A close-up photograph. Located on the leg:
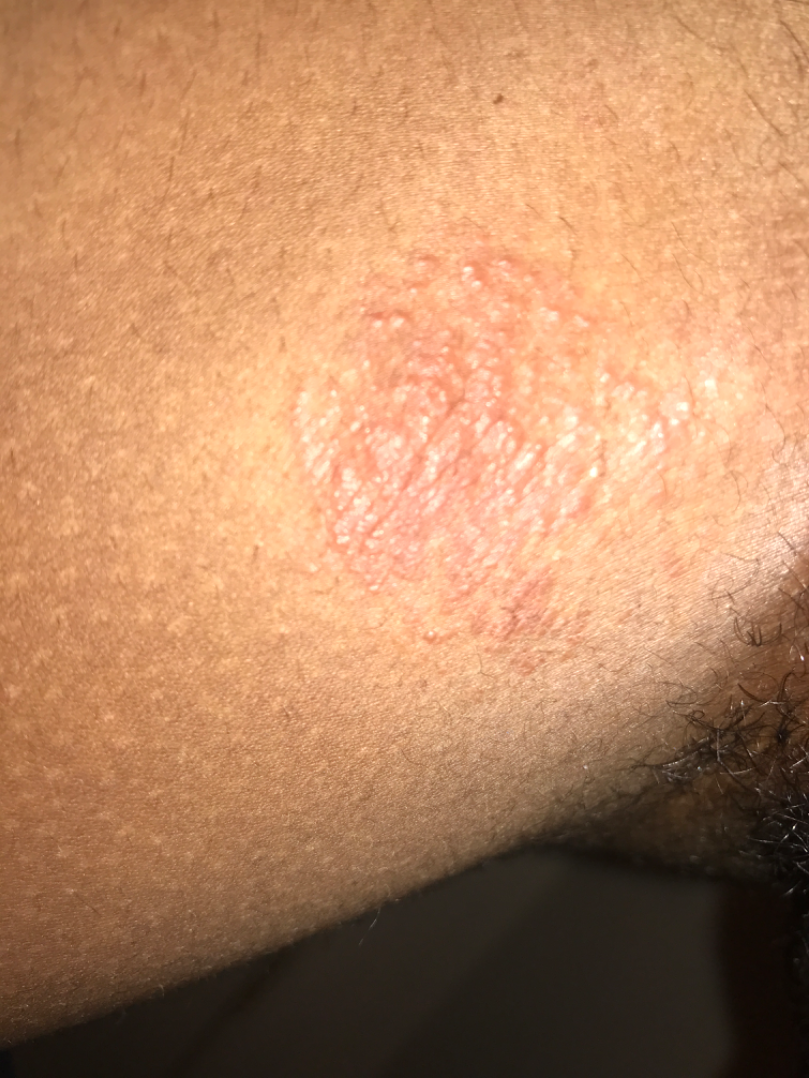Background:
Skin tone: Fitzpatrick V; non-clinician graders estimated Monk skin tone scale 4 or 5 (two reviewer pools). Self-categorized by the patient as a rash. Texture is reported as raised or bumpy. Reported duration is less than one week. The lesion is associated with burning.
Findings:
One reviewing dermatologist: the differential, in no particular order, includes Eczema and Tinea.